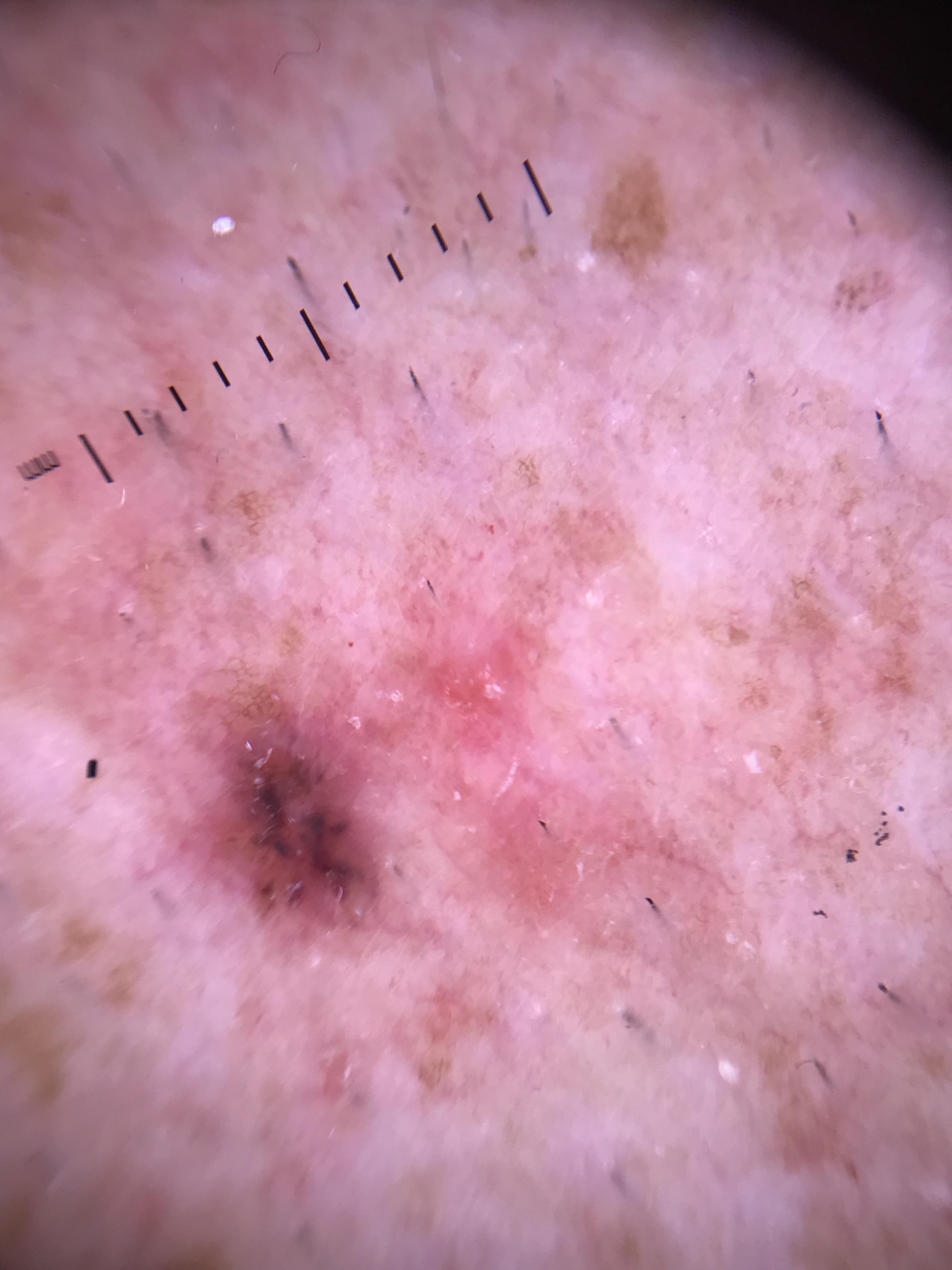Clinical context:
A dermoscopic close-up of a skin lesion. The patient is Fitzpatrick II. A male subject about 55 years old. Located on an upper extremity.
Diagnosis:
Histopathological examination showed a tumor of follicular differentiation — a basal cell carcinoma.